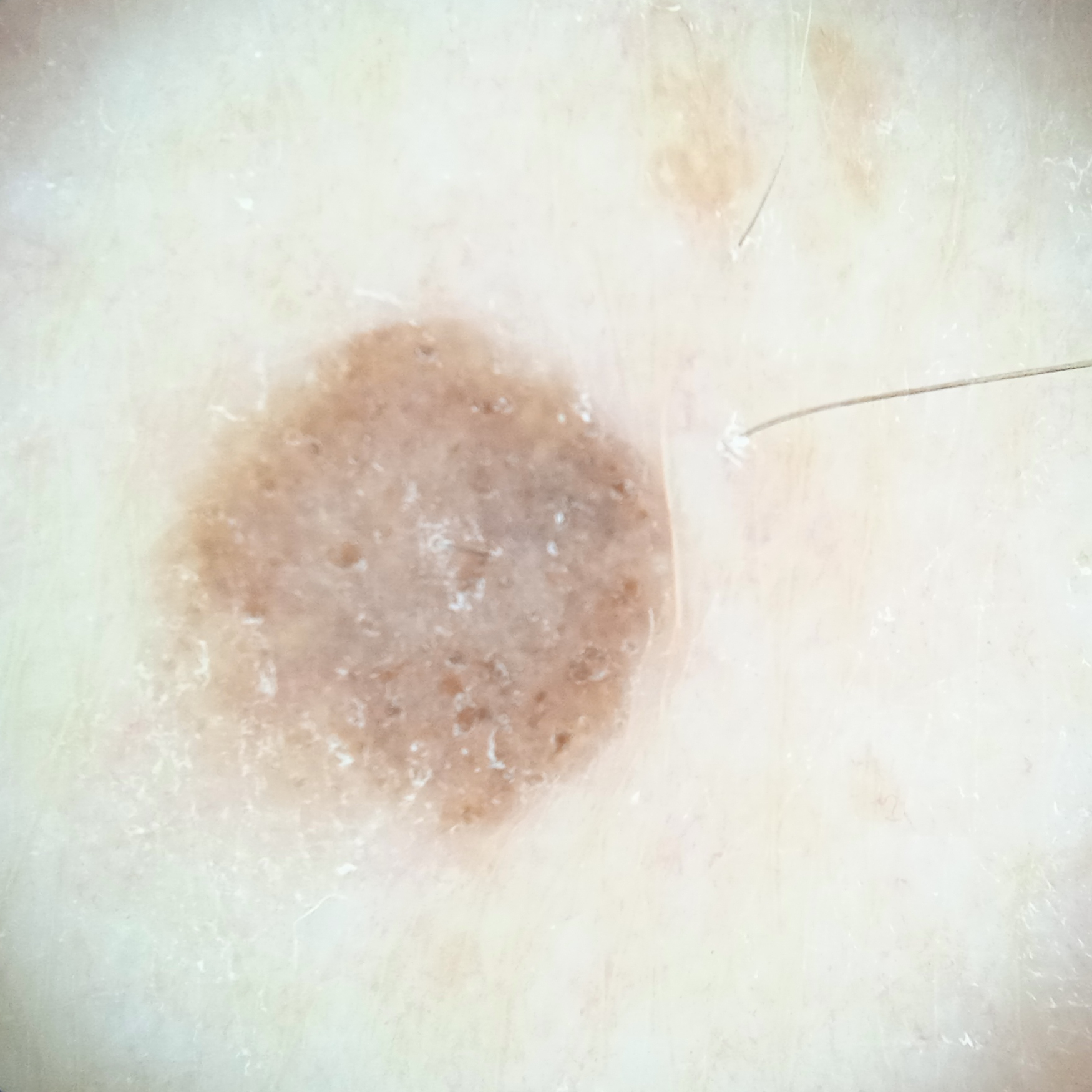Q: Why was this imaged?
A: research study (no referral diagnosis)
Q: Patient demographics?
A: male, age 79
Q: How does the patient's skin react to sun?
A: skin tans without first burning
Q: What is the patient's nevus burden?
A: few melanocytic nevi overall
Q: How large is the lesion?
A: 5.8 mm
Q: What was the diagnosis?
A: melanocytic nevus (dermatologist consensus)